A dermoscopic photograph of a skin lesion:
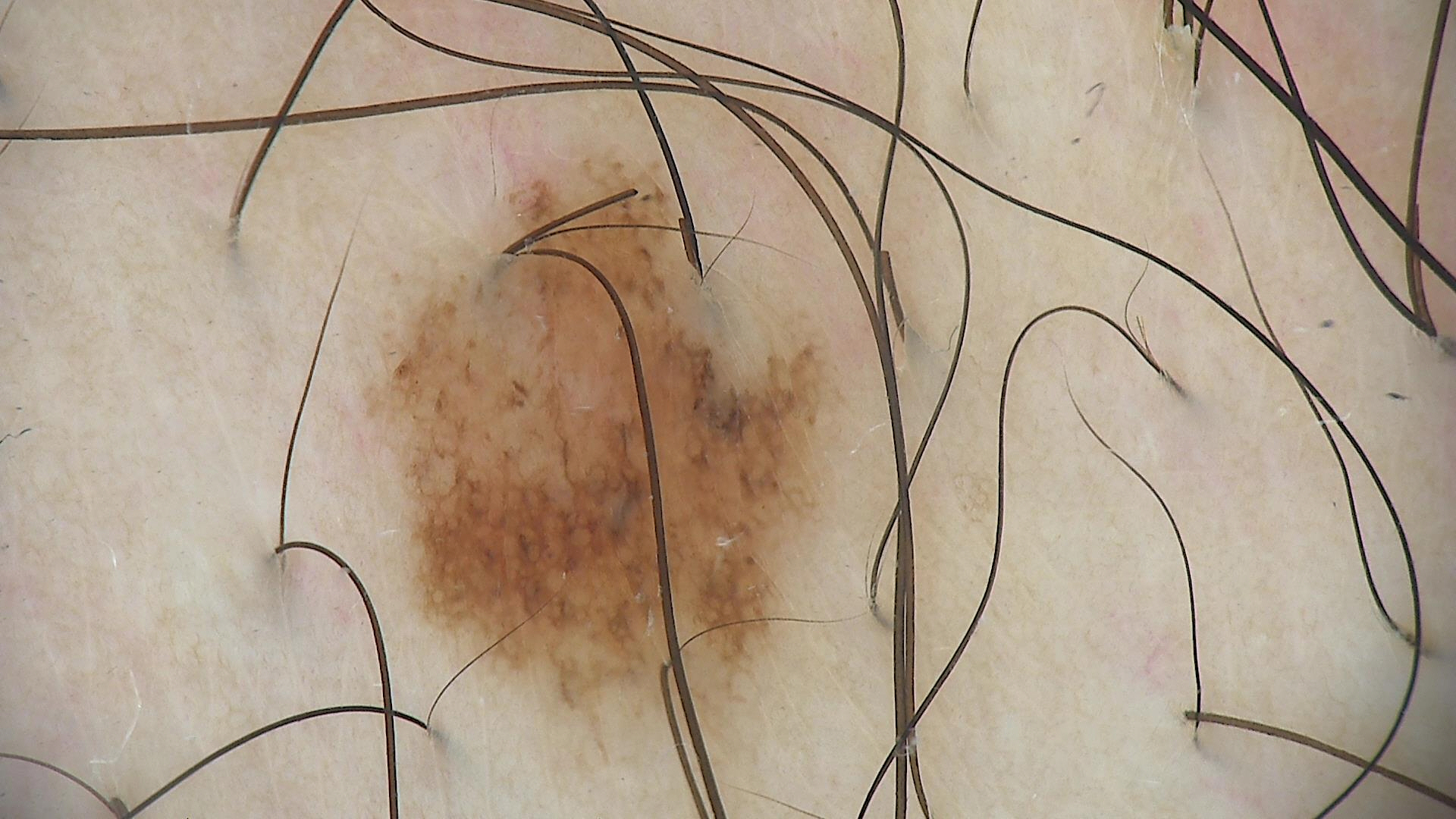Consistent with a dysplastic junctional nevus.